This is a dermoscopic photograph of a skin lesion — 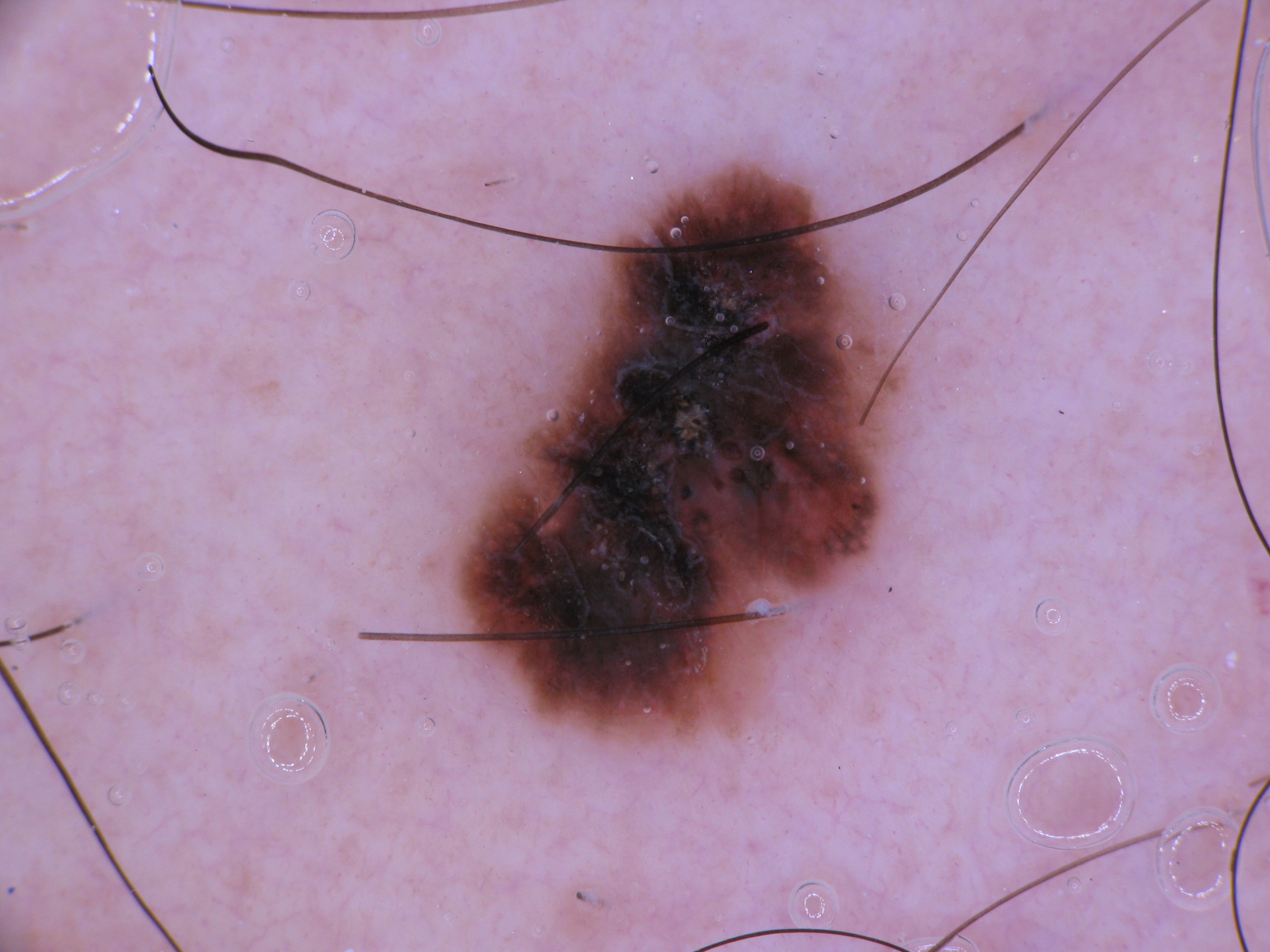| field | value |
|---|---|
| dermoscopic findings | streaks and pigment network; absent: negative network, globules, and milia-like cysts |
| lesion bbox | [447, 162, 903, 749] |
| diagnostic label | a melanoma |